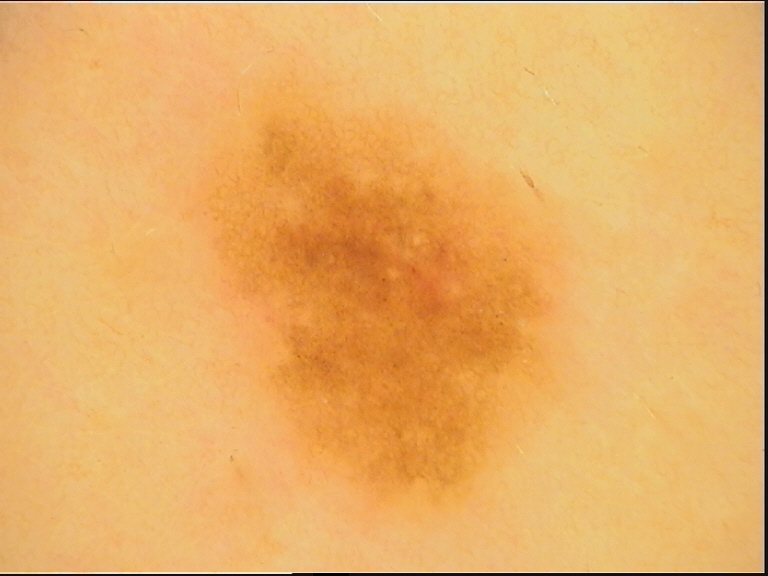Conclusion:
The diagnosis was a banal lesion — a junctional nevus.